A skin lesion imaged with a dermatoscope — 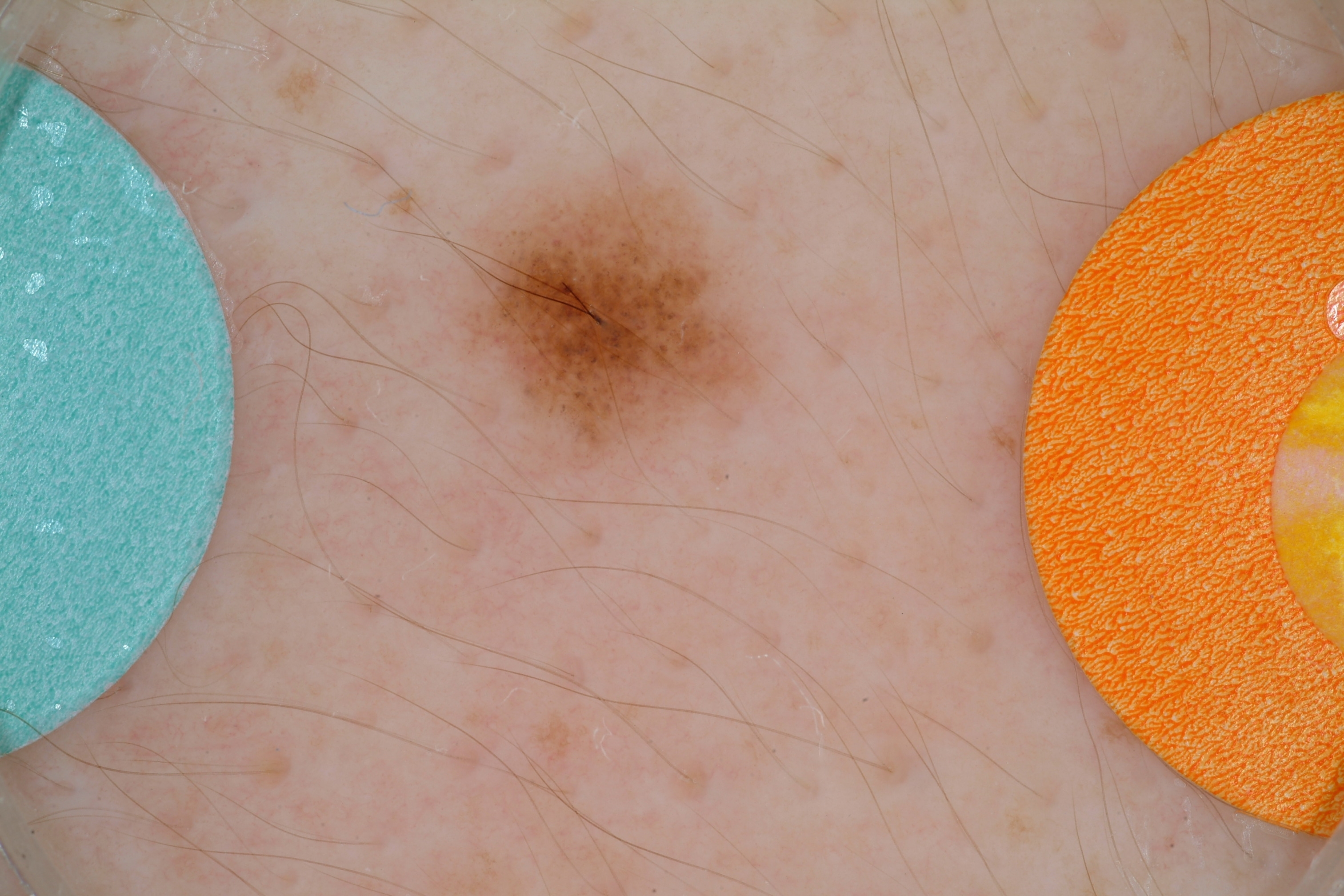Image and clinical context:
Dermoscopic examination shows neither globules nor streaks. In (x1, y1, x2, y2) order, the lesion spans [447, 165, 767, 471]. The lesion covers approximately 5% of the dermoscopic field.
Conclusion:
Expert review diagnosed this as a benign lesion.